The patient says their skin reddens painfully with sun exposure; by self-report, immunosuppression and a prior organ transplant; a moderate number of moles by the patient's own estimate; collected as part of a research study, without a referral diagnosis; a female patient age 55; dermoscopy of a skin lesion:
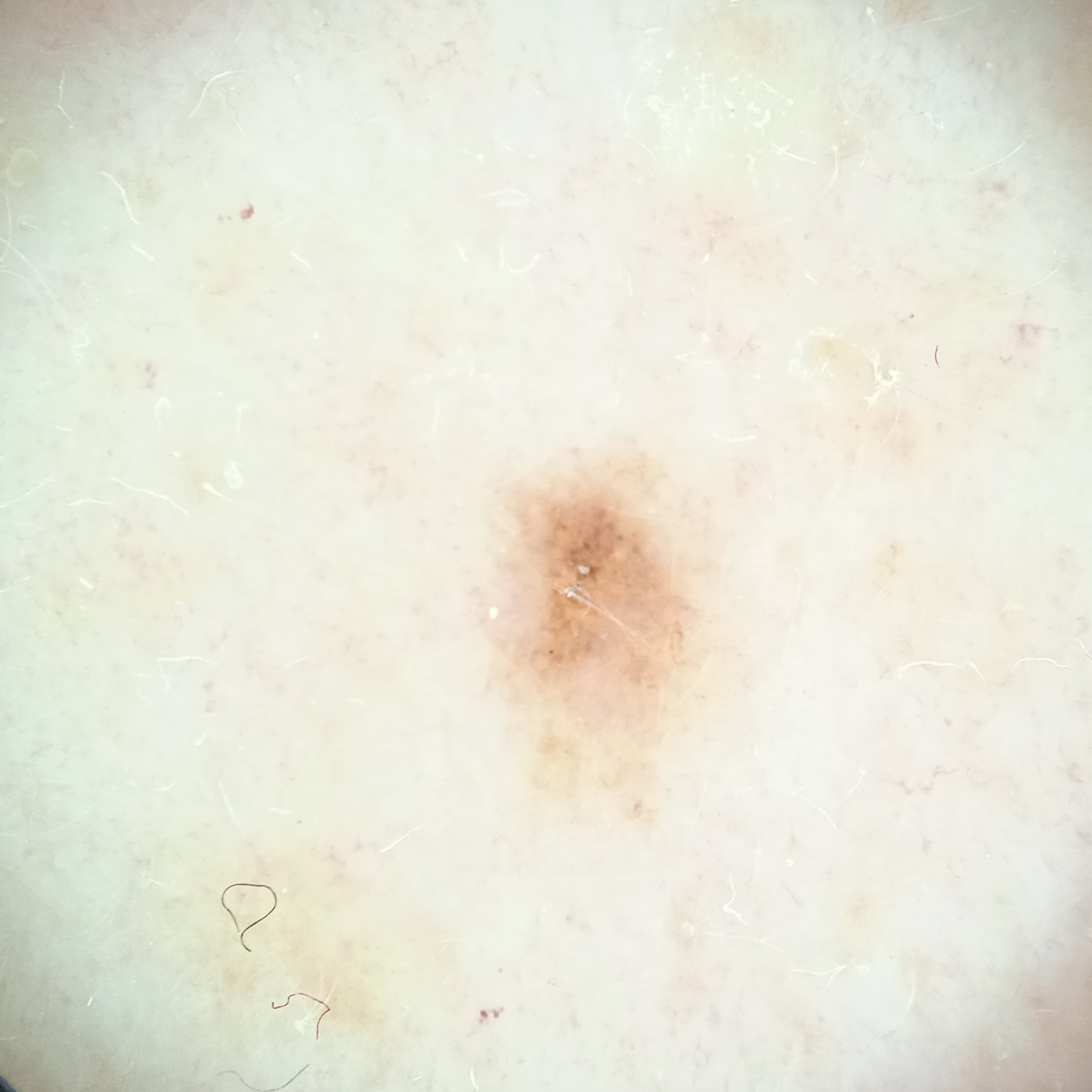The lesion is on the back.
The lesion is about 2.5 mm across.
The dermatologists' assessment was a melanocytic nevus.